Close-up view:
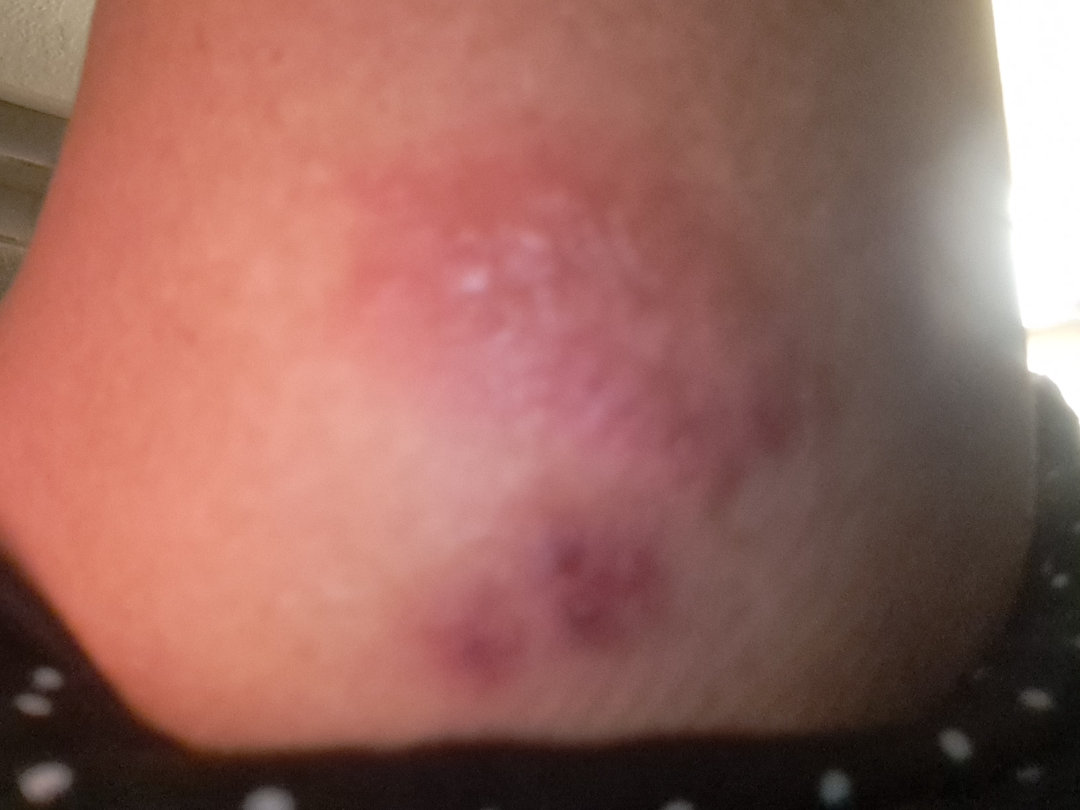Notes:
• assessment — indeterminate